A contact-polarized dermoscopy image of a skin lesion. The chart records a first-degree relative with melanoma. The patient is Fitzpatrick phototype III.
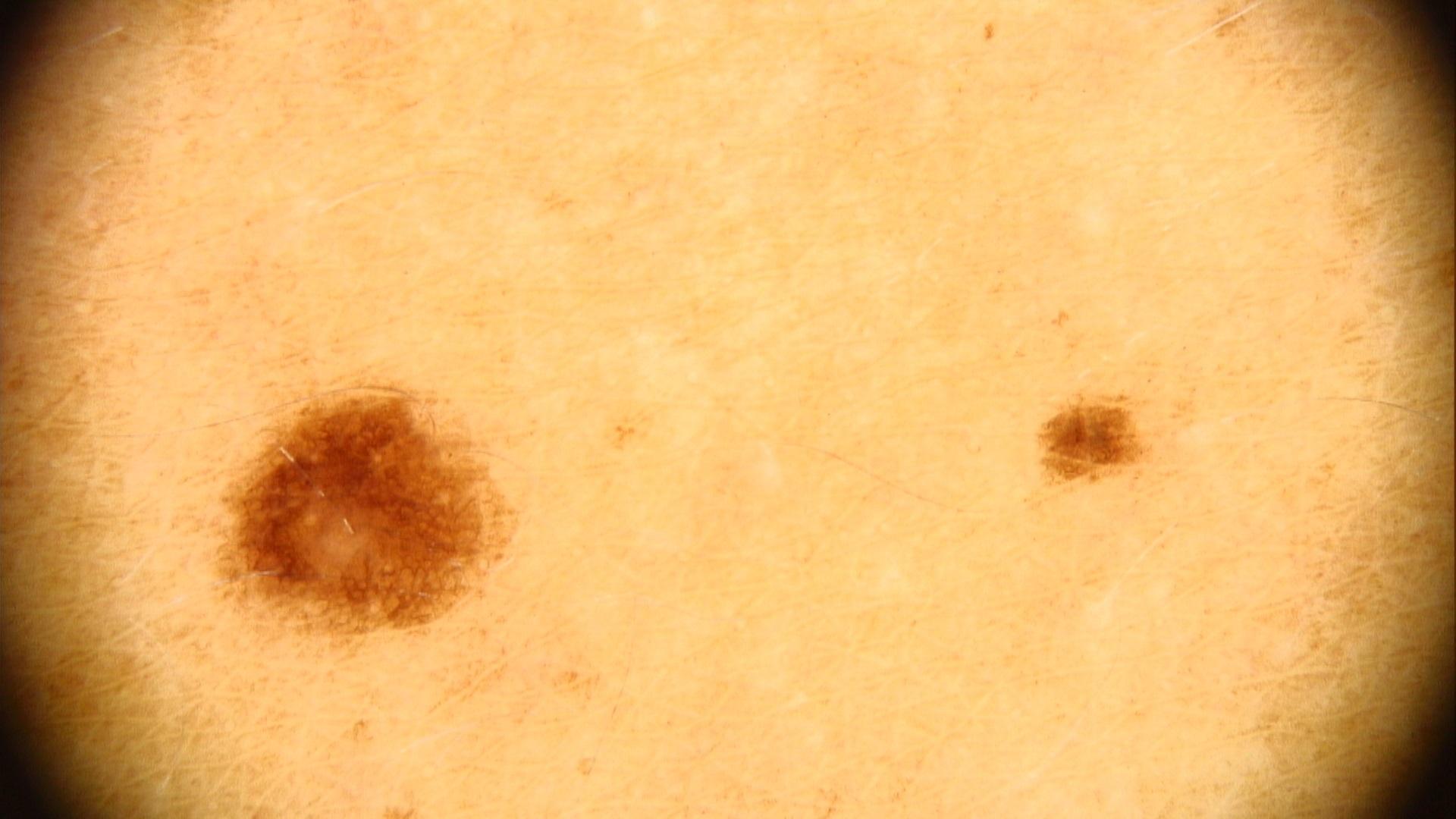• site · the trunk
• assessment · Nevus